The photo was captured at a distance. Fitzpatrick phototype IV; lay graders estimated 4 on the MST. The lesion is described as flat and rough or flaky. The condition has been present for about one day. Located on the leg. No relevant systemic symptoms. The patient is 30–39, female.
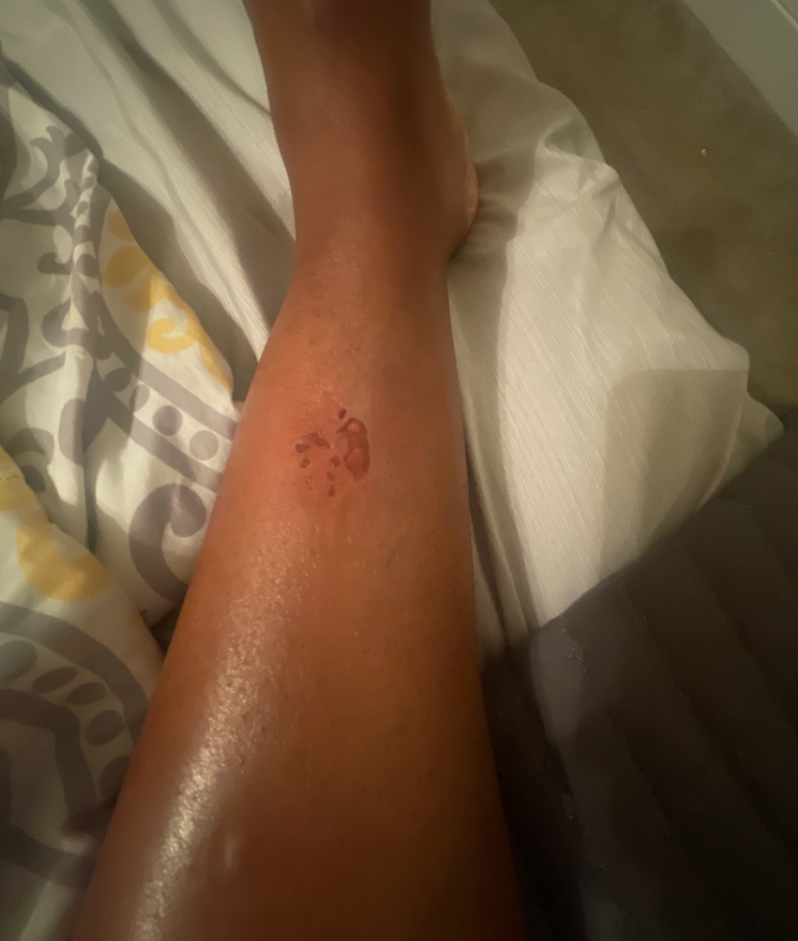Stasis Dermatitis (considered); Abrasion, scrape, or scab (considered); Bullosis diabeticorum (unlikely); Allergic Contact Dermatitis (unlikely).